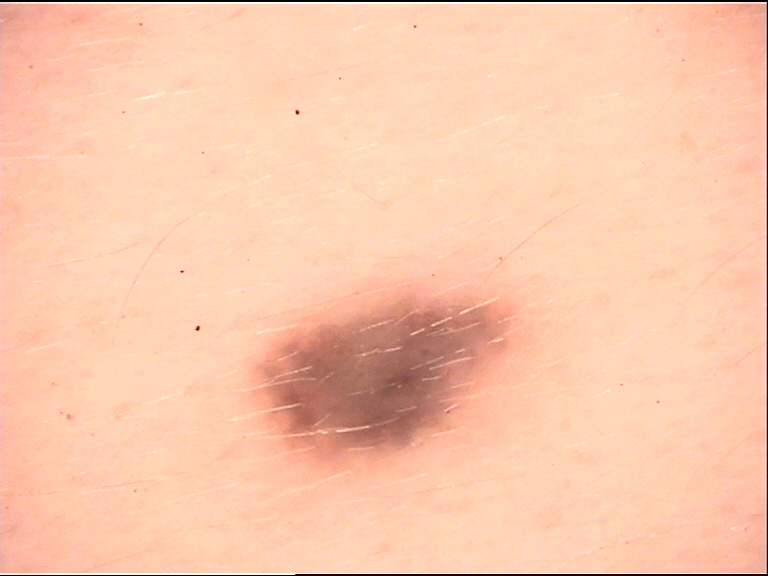This is a dermal, banal lesion. Consistent with a blue nevus.